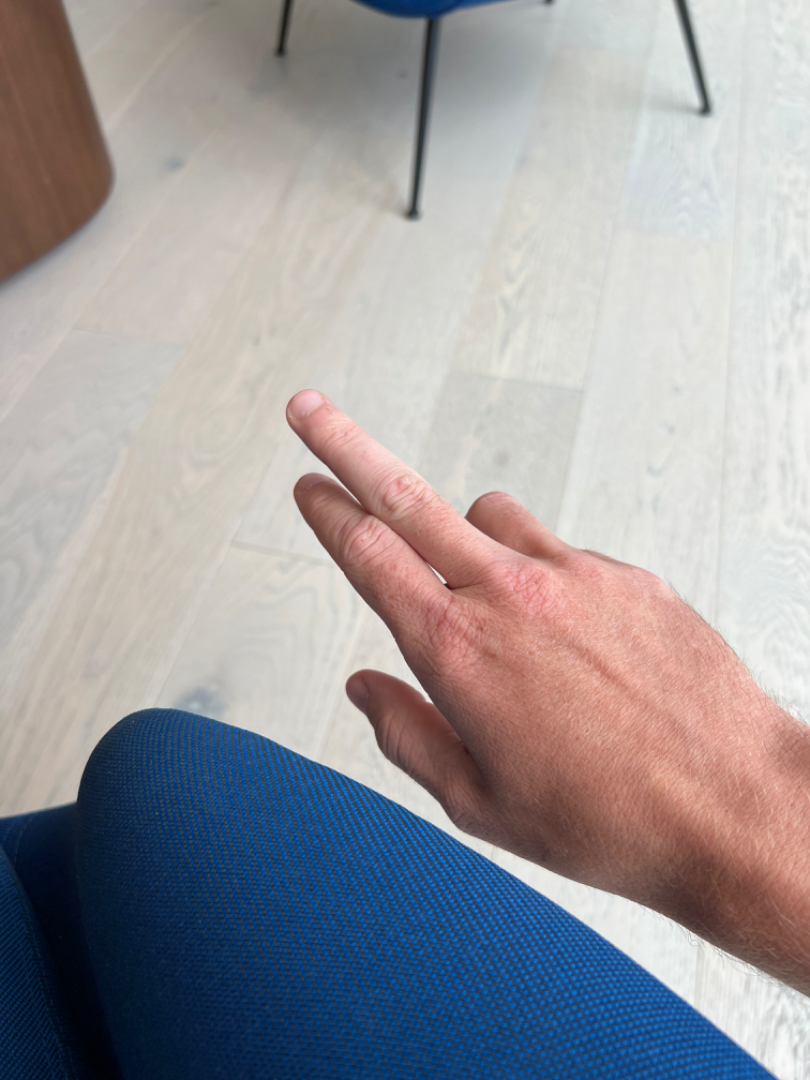Q: Image view?
A: at a distance
Q: Anatomic location?
A: back of the hand
Q: What is the differential diagnosis?
A: most consistent with Verruca vulgaris